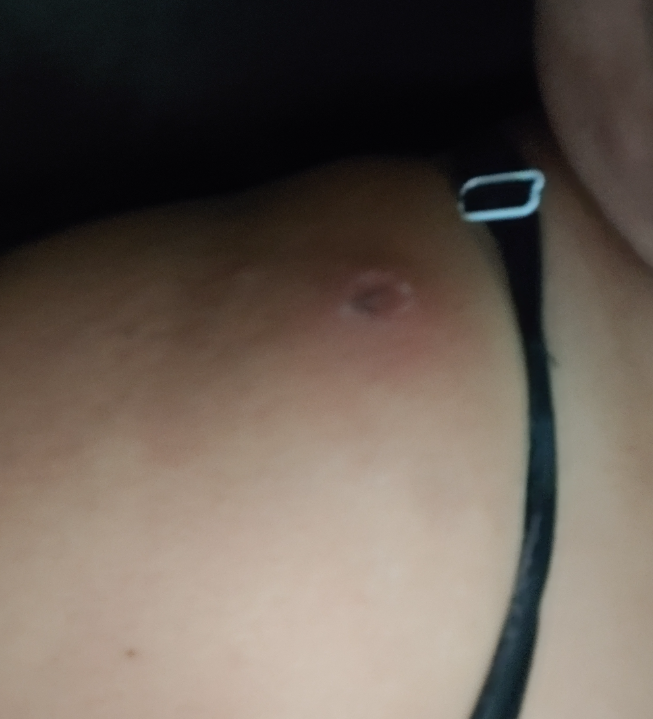Impression: The condition could not be reliably identified from the image. History: The patient considered this a rash. Female patient, age 40–49. The condition has been present for about one day. The lesion is associated with itching and bothersome appearance. Close-up view. Texture is reported as fluid-filled.